The condition has been present for about one day · the contributor notes itching · the patient described the issue as a rash · this is a close-up image · the lesion is described as raised or bumpy · no constitutional symptoms were reported — 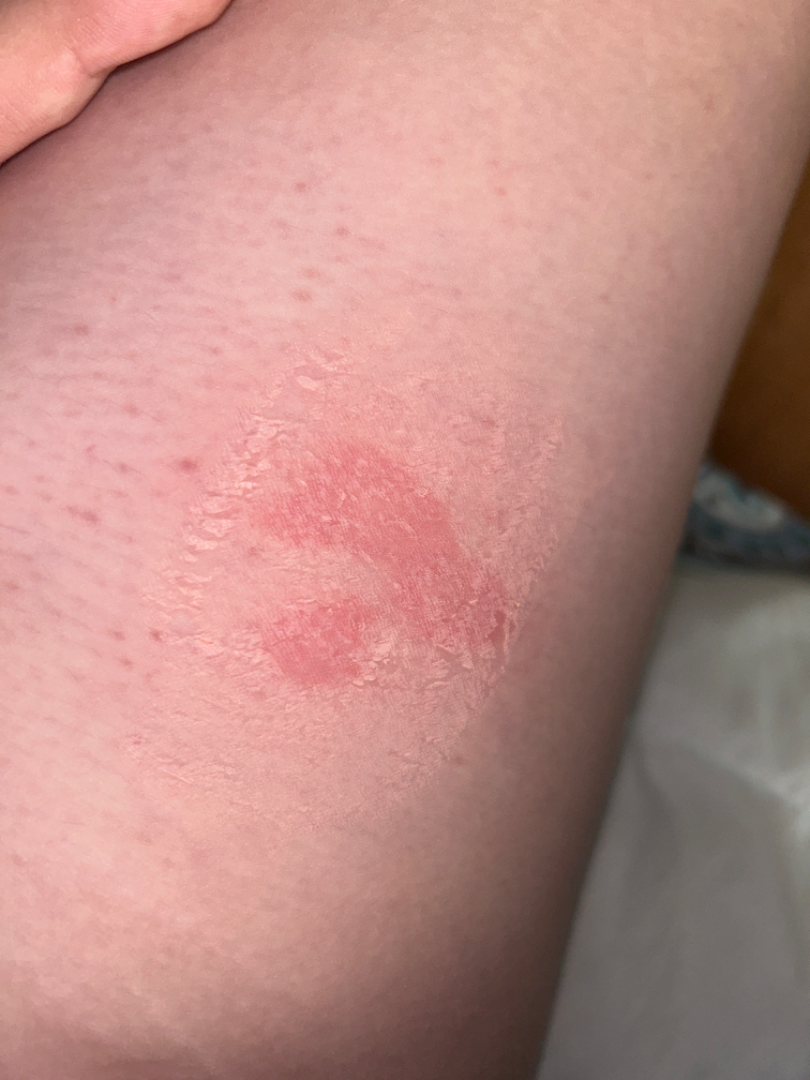clinical impression: Eczema (considered); Allergic Contact Dermatitis (considered); Irritant Contact Dermatitis (considered).